A moderate number of moles by the patient's own estimate. The patient says their skin reddens with sun exposure. Dermoscopy of a skin lesion. A male subject aged 77. Collected as part of a research study, without a referral diagnosis. On a questionnaire the patient reported a personal history of skin cancer and a personal history of cancer: 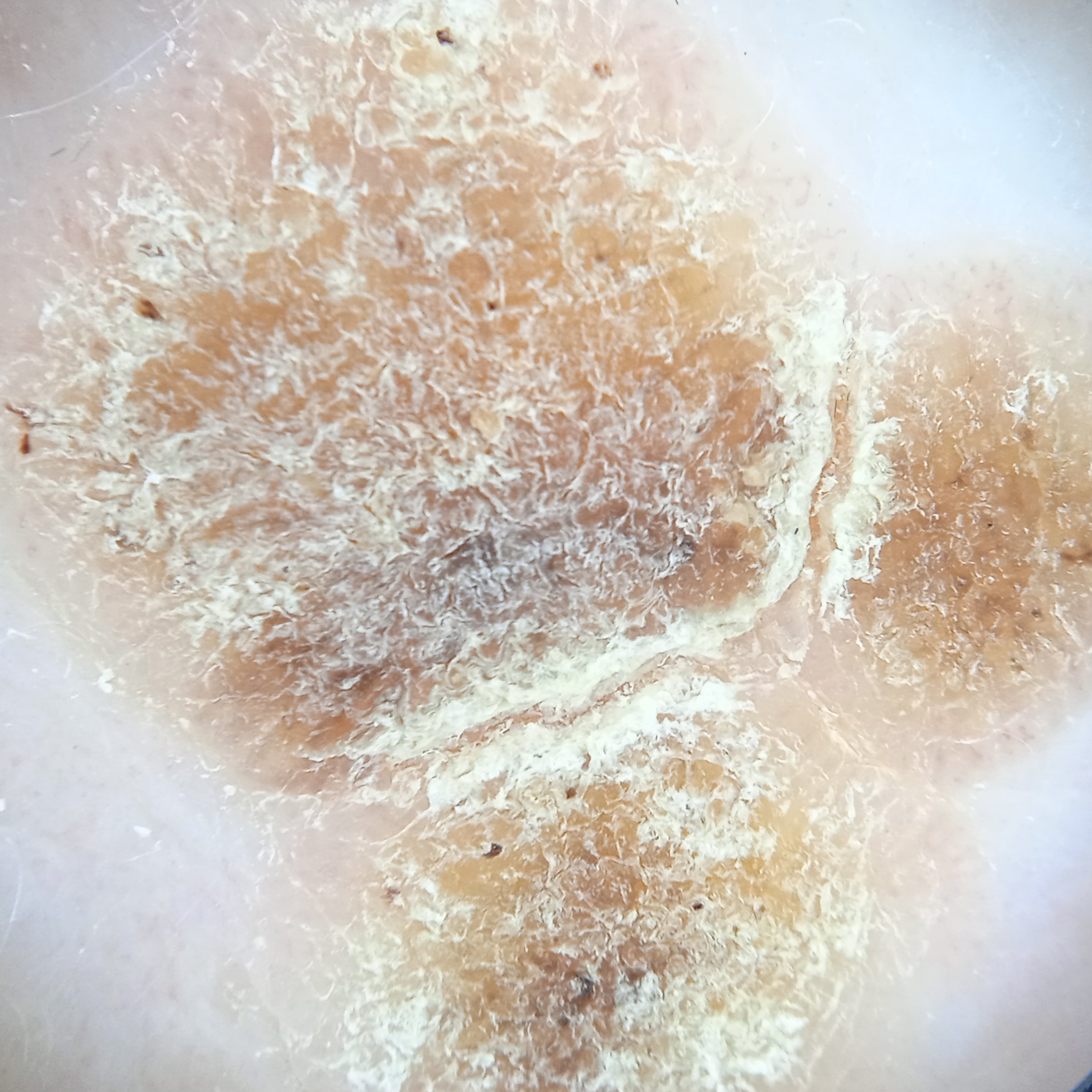Measuring roughly 14.2 mm.
The consensus diagnosis for this lesion was a seborrheic keratosis.